Dermoscopy of a skin lesion:
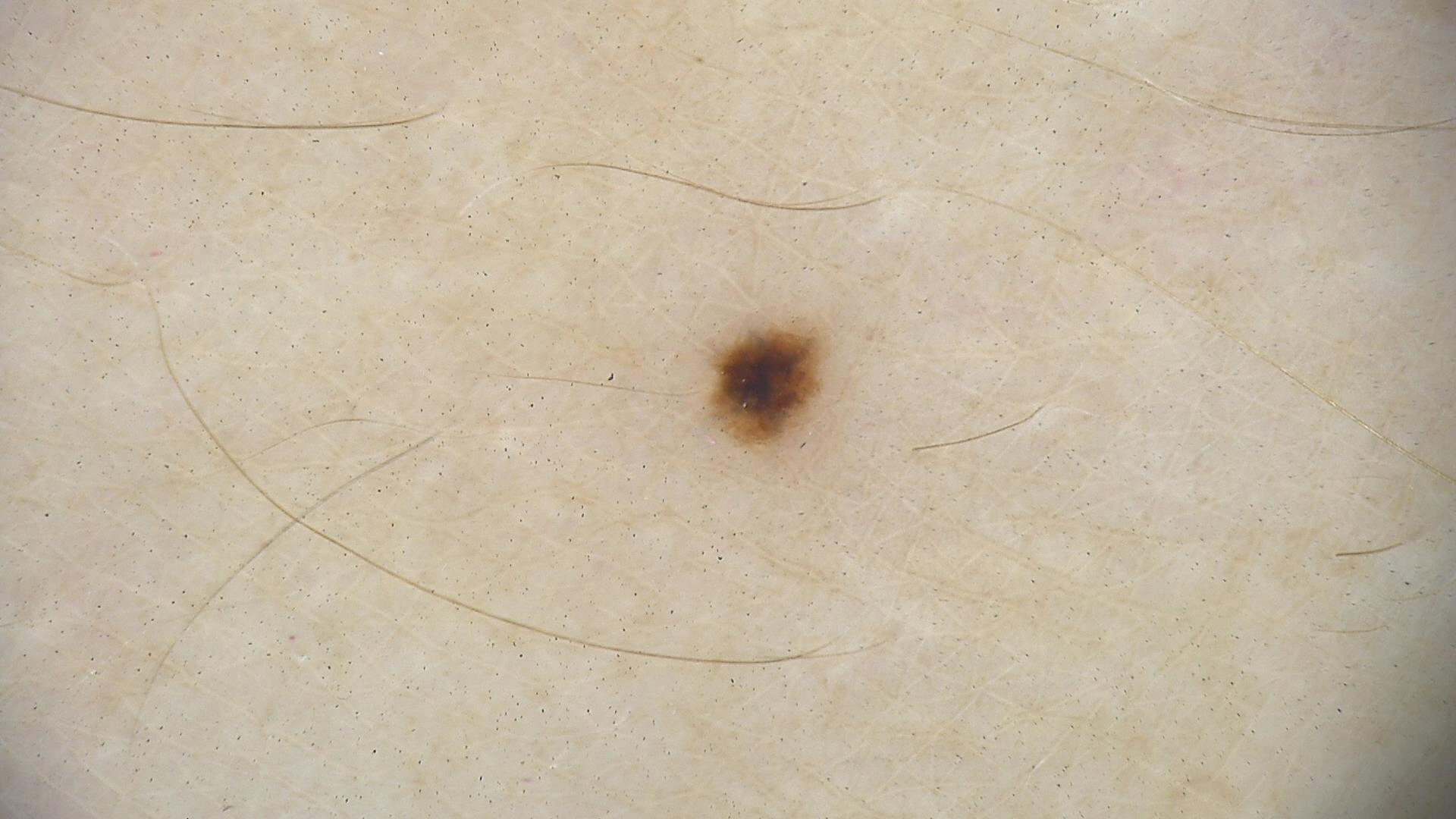Diagnosed as a dysplastic junctional nevus.